A dermoscopic close-up of a skin lesion.
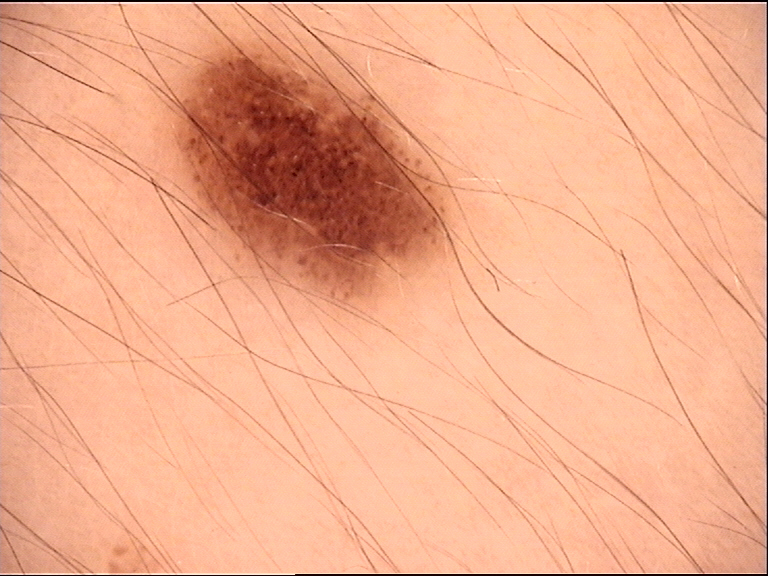{"lesion_type": {"main_class": "banal", "pattern": "junctional"}, "diagnosis": {"name": "junctional nevus", "code": "jb", "malignancy": "benign", "super_class": "melanocytic", "confirmation": "expert consensus"}}